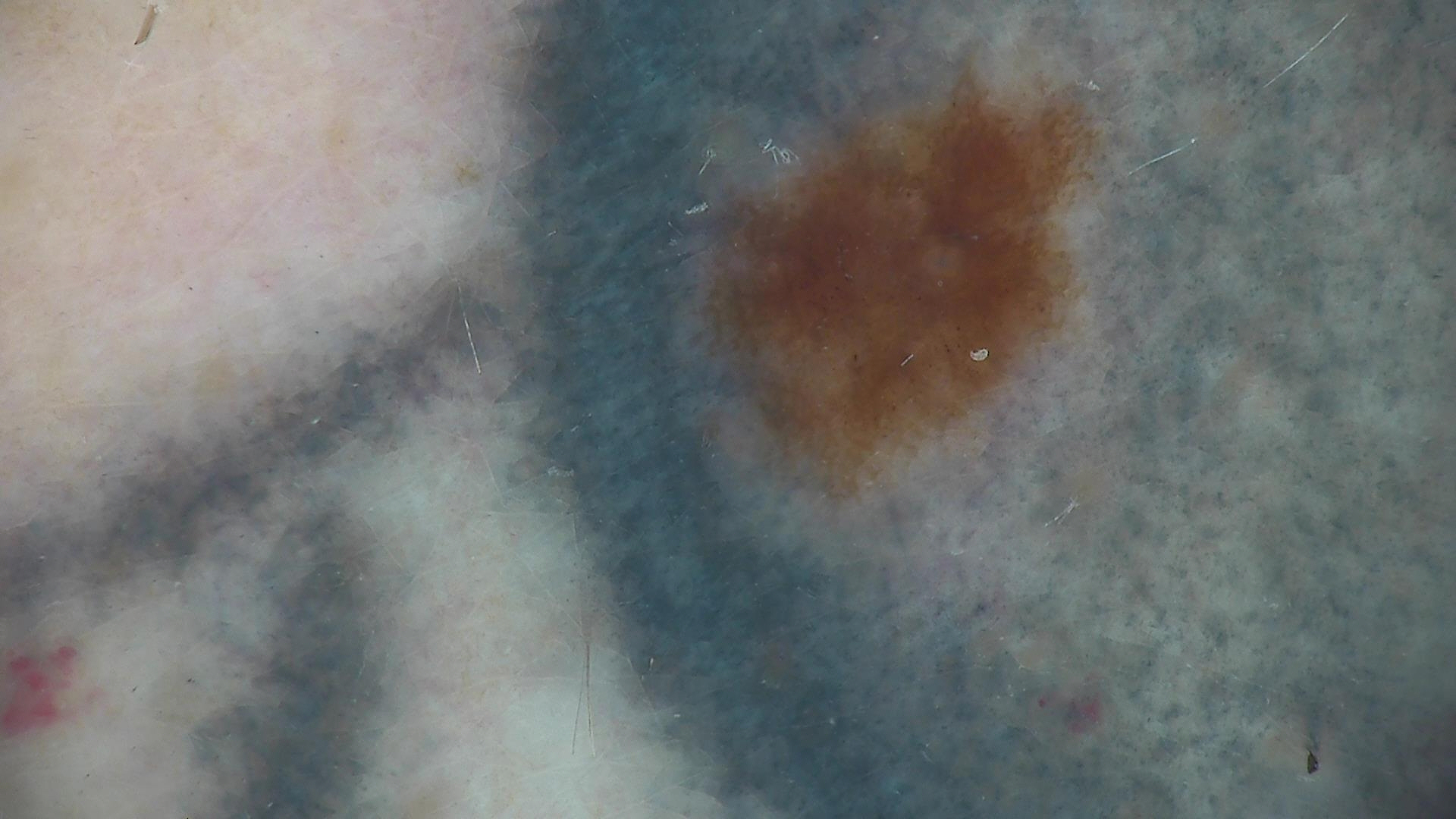Dermoscopy of a skin lesion. The diagnostic label was a benign lesion — a dysplastic junctional nevus.